A male patient approximately 65 years of age. A dermoscopic view of a skin lesion: 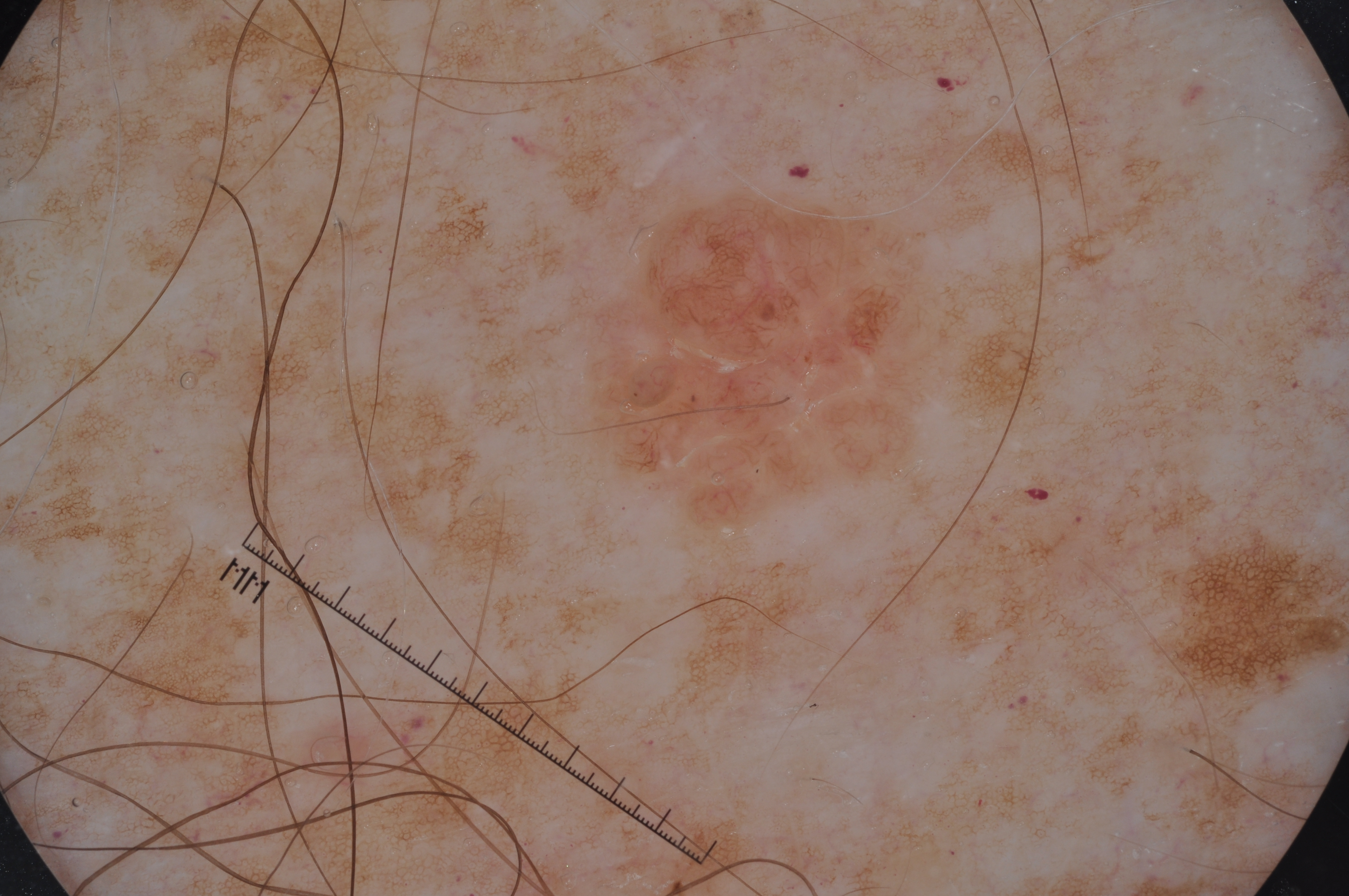lesion size — moderate
dermoscopic pattern — pigment network
lesion bbox — 556/191/953/537
diagnostic label — a melanocytic nevus, a benign skin lesion